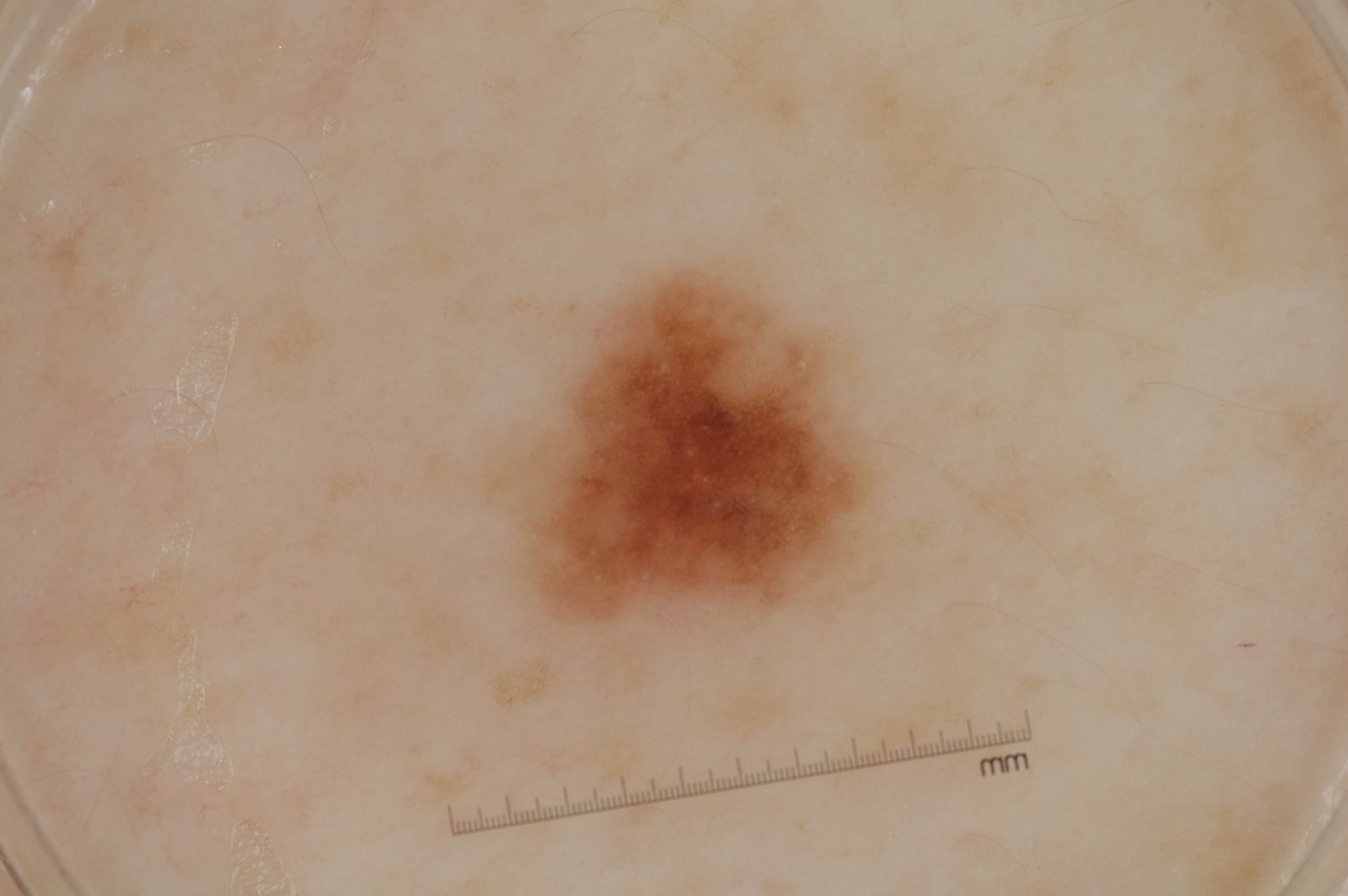imaging = dermoscopy | patient = female, aged 28 to 32 | lesion location = [506,266,874,623] | dermoscopic features = pigment network and milia-like cysts | diagnosis = a melanocytic nevus.